A dermoscopic close-up of a skin lesion · a male subject in their 40s.
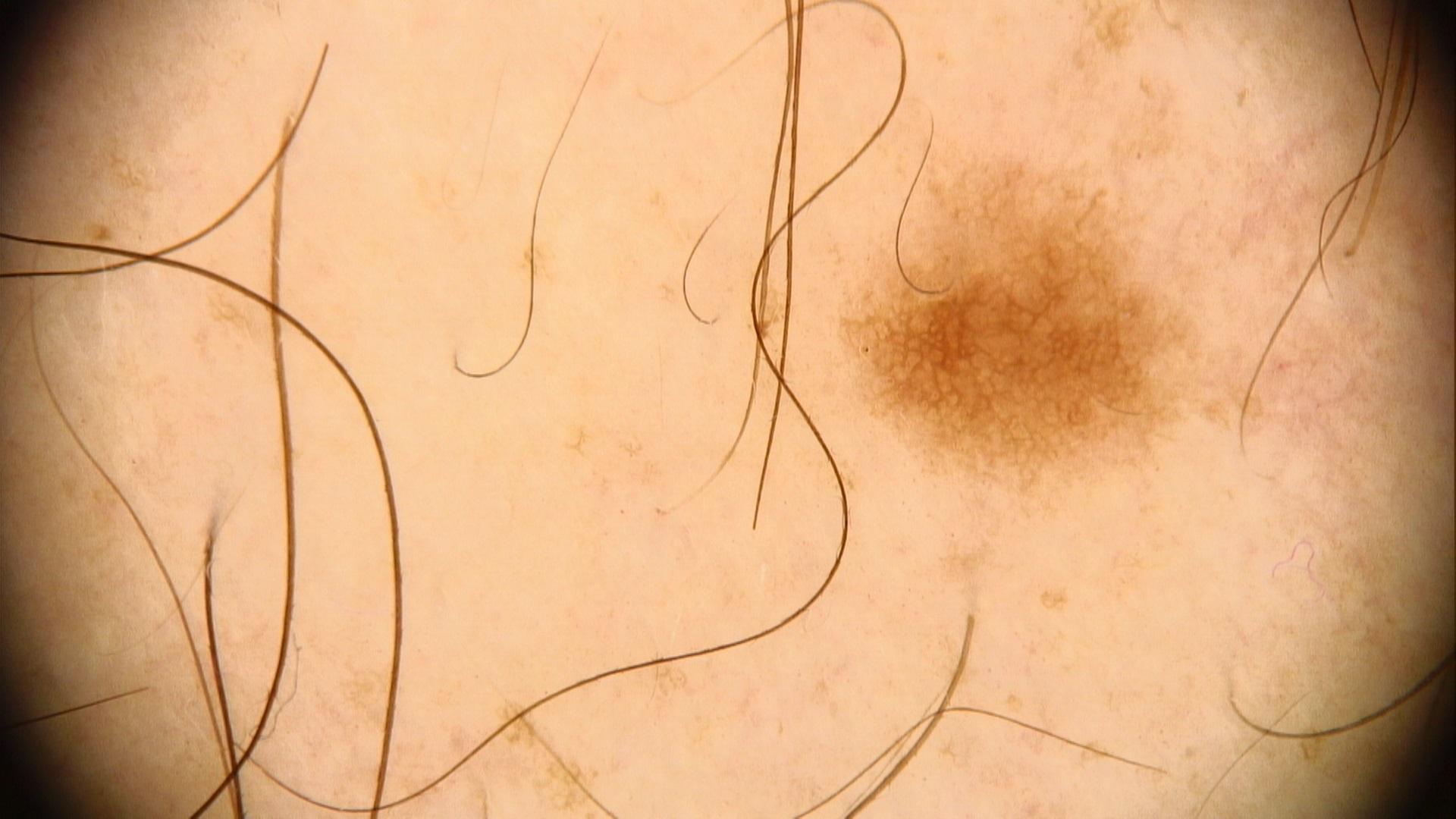Case:
• assessment · Nevus